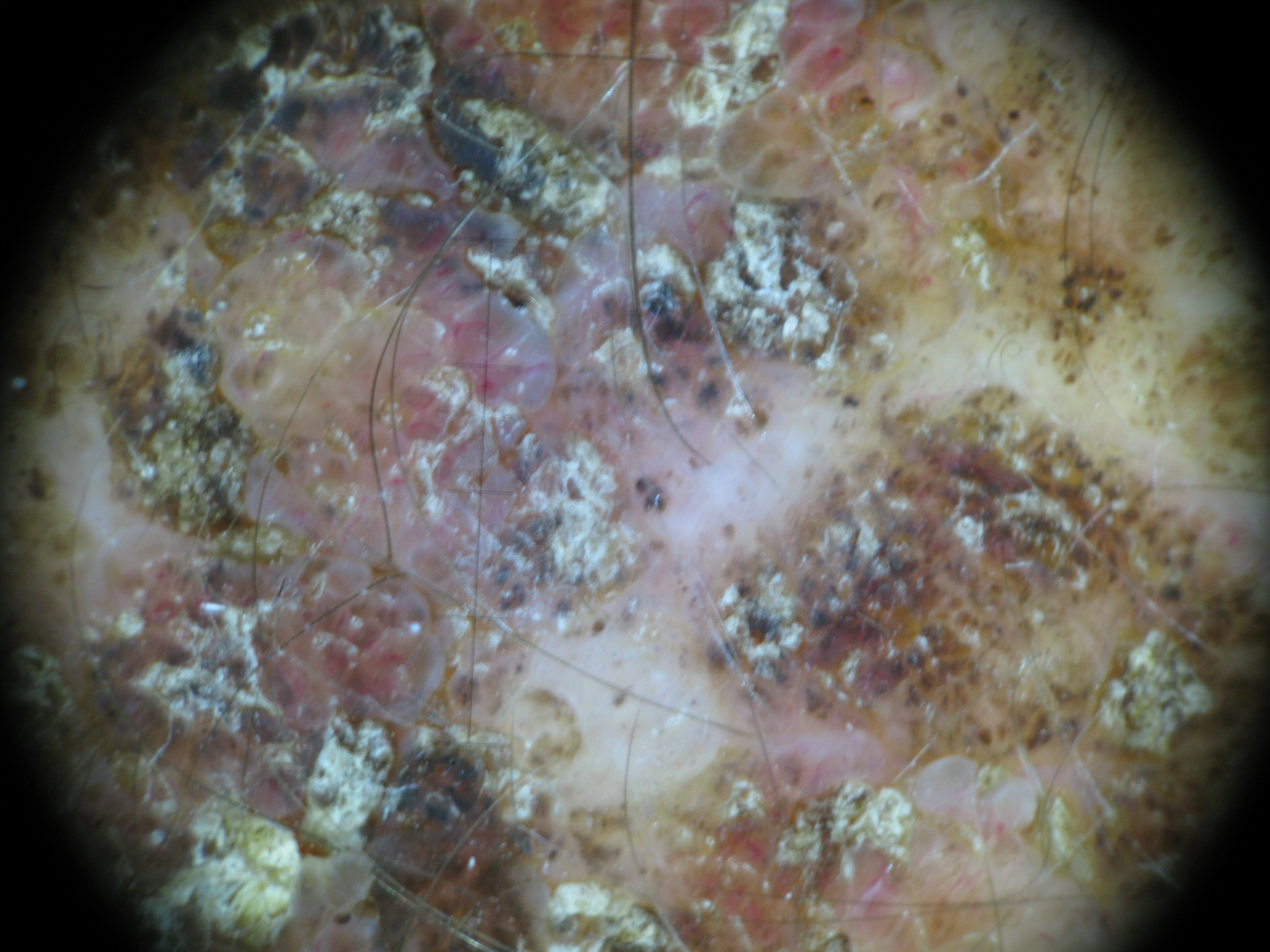<case>
<image>dermoscopy</image>
<diagnosis>
<name>melanoma</name>
<code>mel</code>
<malignancy>malignant</malignancy>
<super_class>melanocytic</super_class>
<confirmation>histopathology</confirmation>
</diagnosis>
</case>